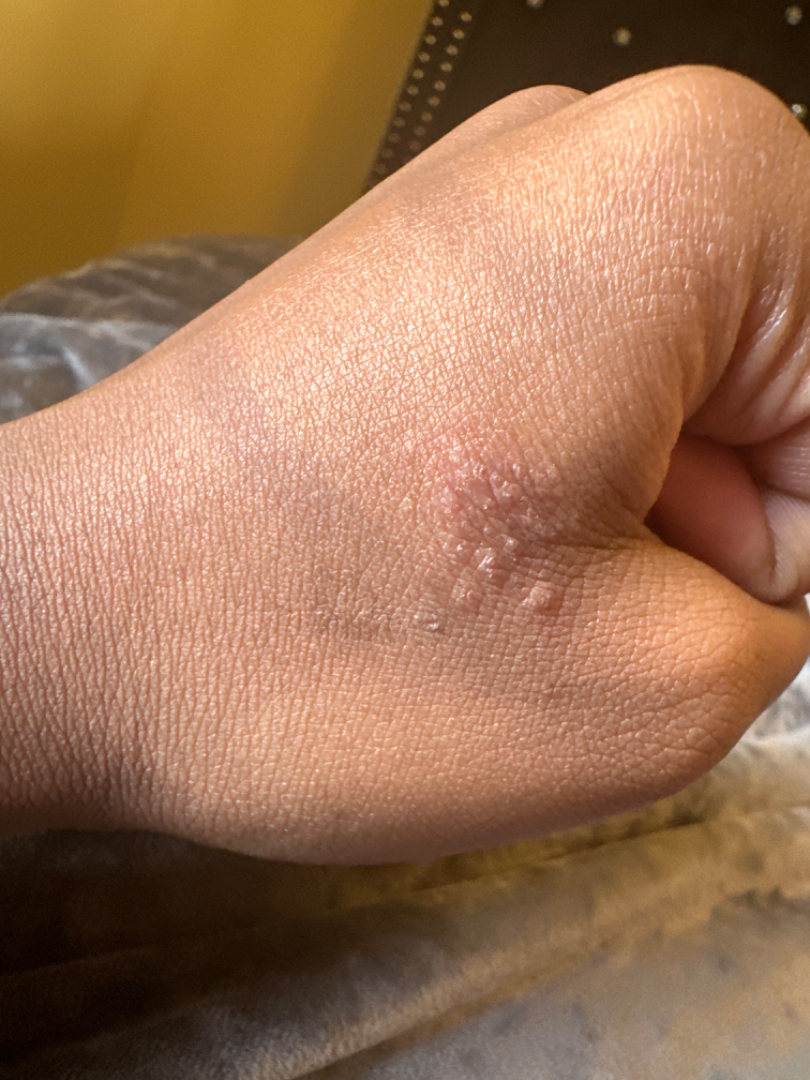Acute and chronic dermatitis (33%); Allergic Contact Dermatitis (33%); Irritant Contact Dermatitis (33%).